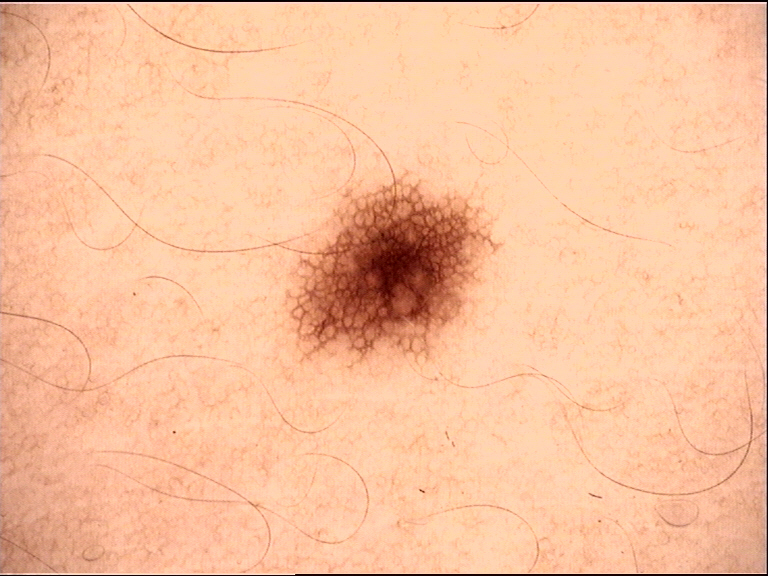Impression: The diagnosis was a dysplastic junctional nevus.